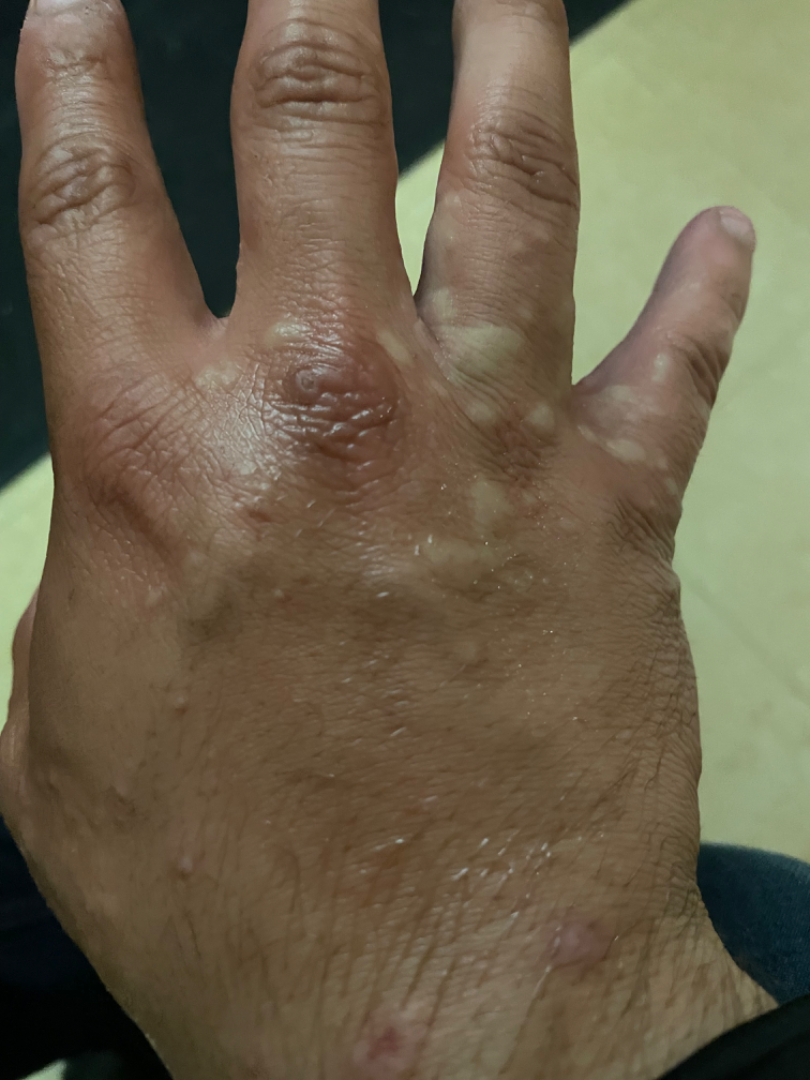symptom duration = less than one week | location = back of the torso, front of the torso, arm and back of the hand | shot type = at an angle | differential diagnosis = the impression was split between Eczema and Acute dermatitis, NOS.